A skin lesion imaged with a dermatoscope.
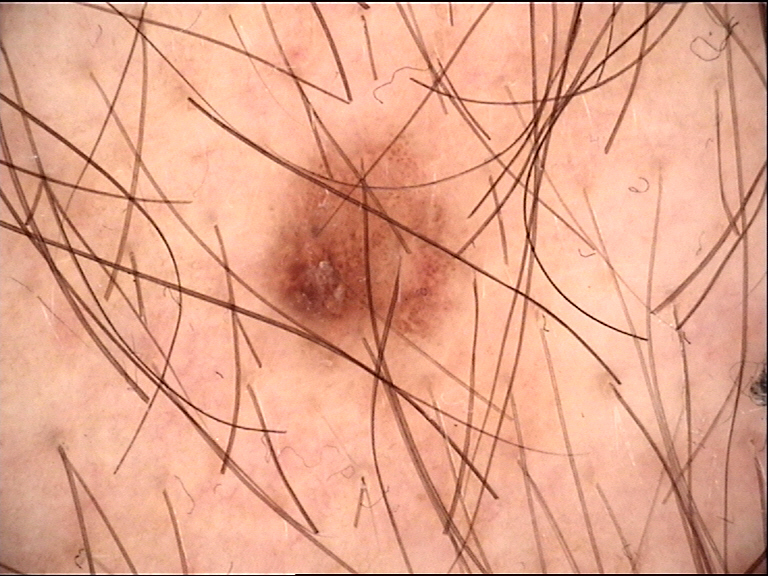Impression:
Consistent with a banal lesion — a junctional nevus.